The affected area is the head or neck · the patient is 40–49, female · close-up view: 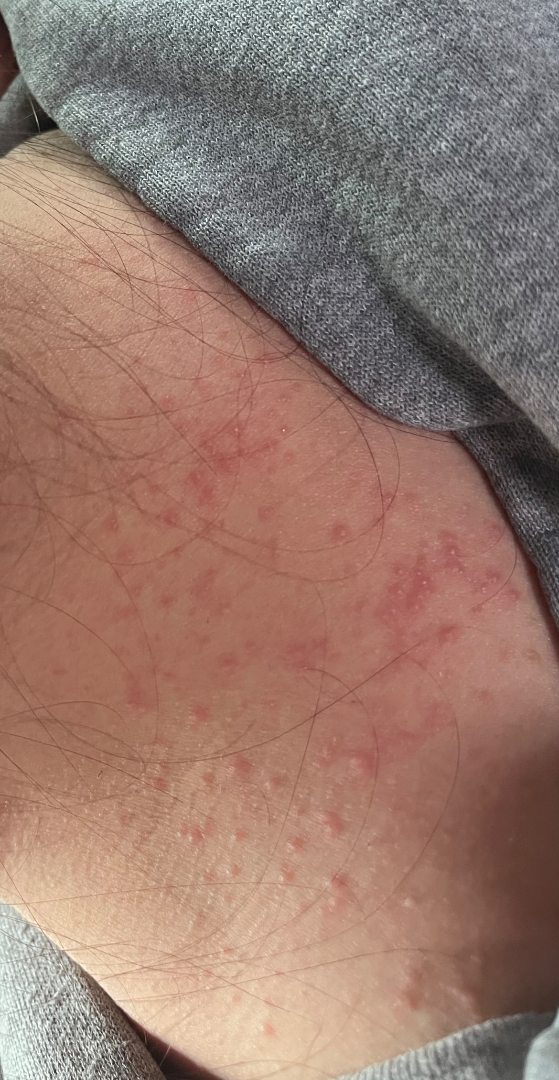{
  "assessment": "indeterminate from the photograph"
}